Located on the back of the torso. The patient described the issue as a rash. Male subject, age 30–39. This is a close-up image. Texture is reported as raised or bumpy. Skin tone: self-reported Fitzpatrick phototype I. Reported lesion symptoms include itching, burning and pain. The condition has been present for less than one week:
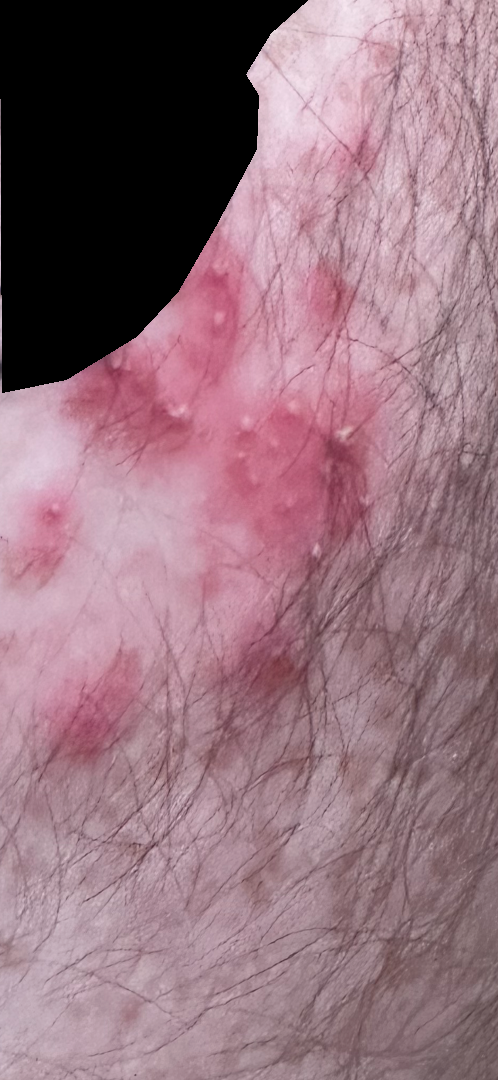The skin findings could not be characterized from the image.